A dermoscopic photograph of a skin lesion.
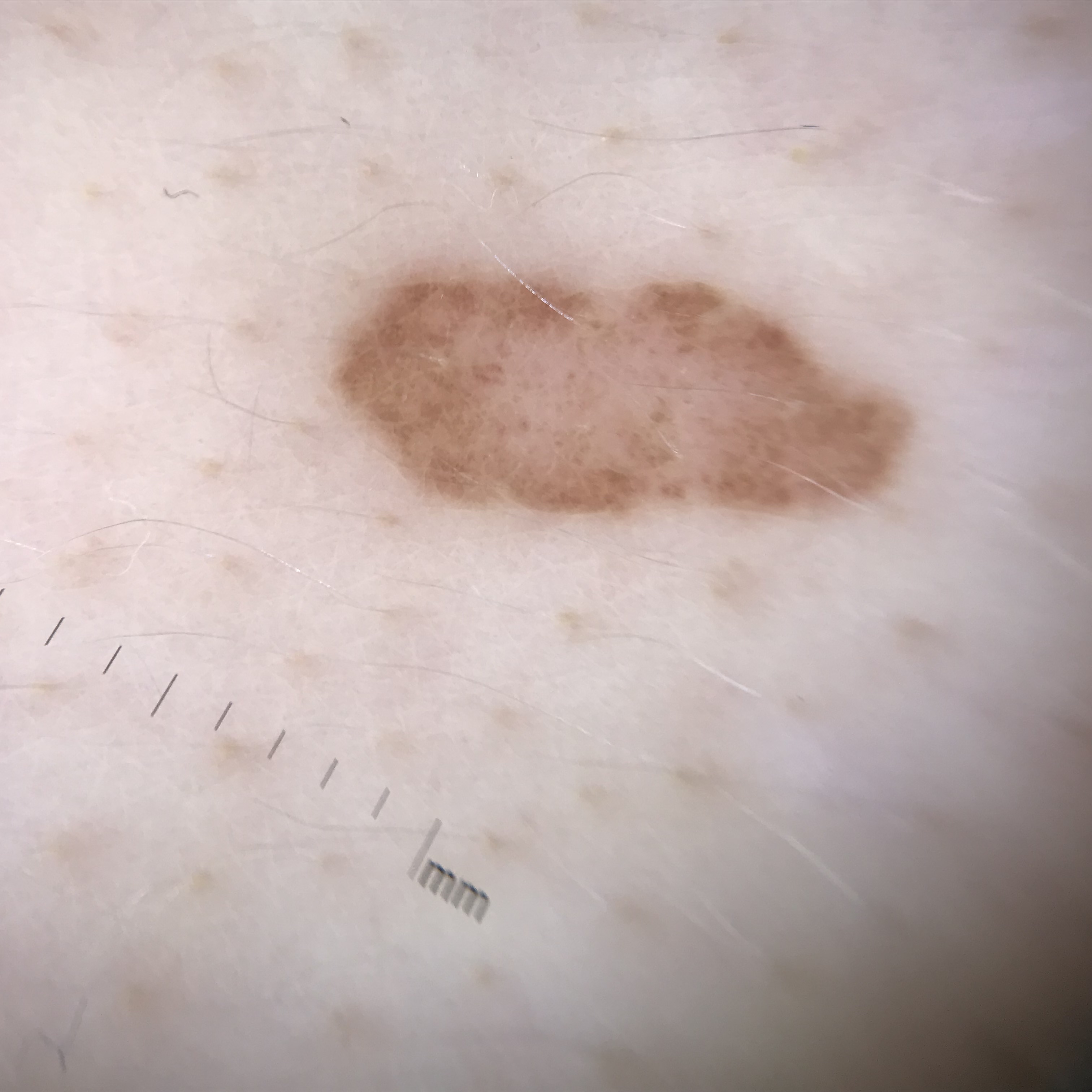Conclusion:
Diagnosed as a benign lesion — a dysplastic compound nevus.